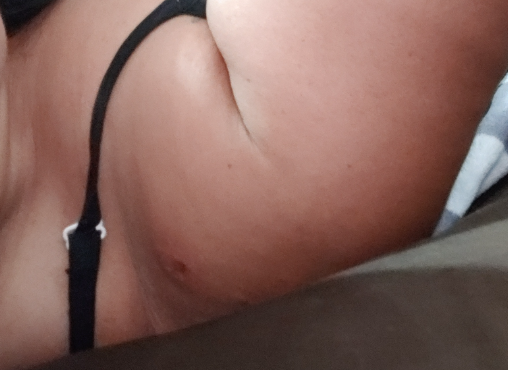Findings:
The dermatologist could not determine a likely condition from the photograph alone.
Background:
This image was taken at a distance. The subject is 40–49, female.